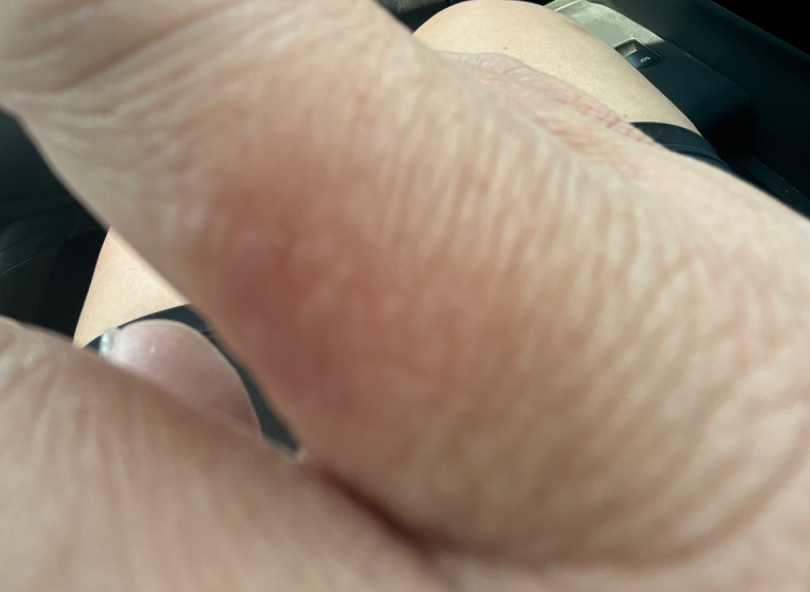Q: What was the assessment?
A: unable to determine
Q: Image view?
A: at an angle